A dermoscopy image of a single skin lesion:
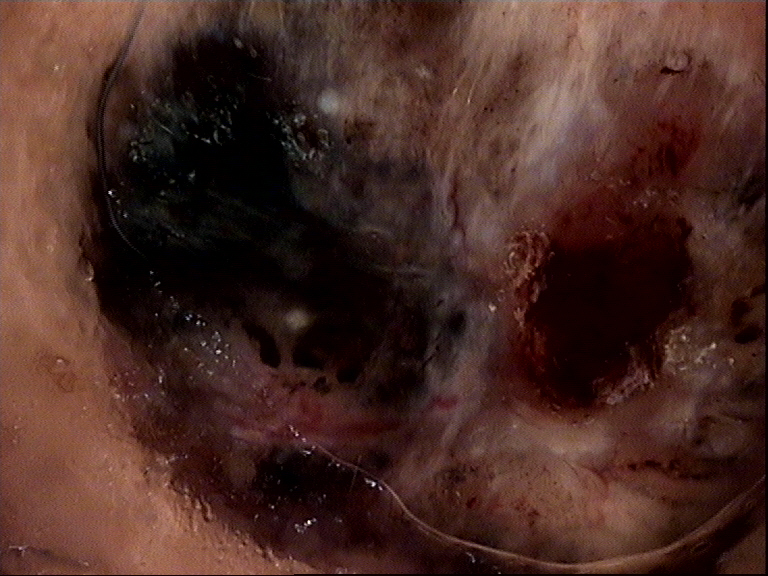Q: What did the workup show?
A: basal cell carcinoma (biopsy-proven)